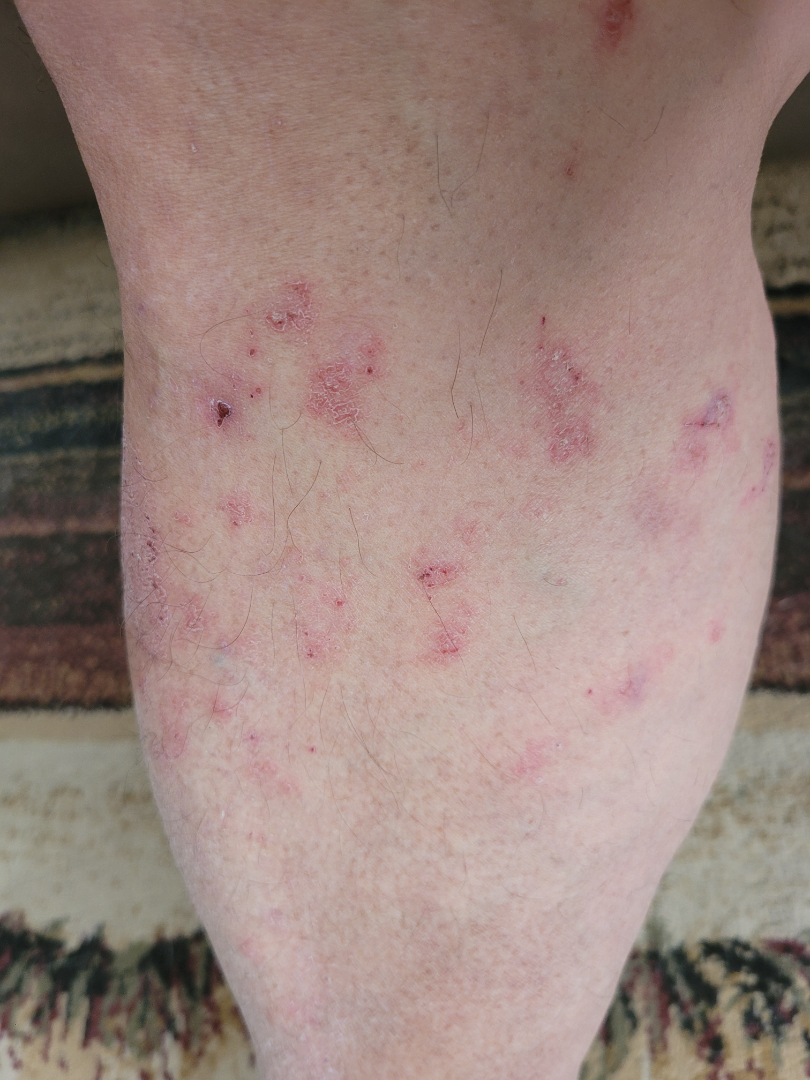• systemic symptoms: none reported
• contributor: male, age 60–69
• photo taken: at an angle
• described texture: raised or bumpy
• anatomic site: leg
• patient describes the issue as: a rash
• symptom duration: less than one week
• lesion symptoms: itching
• assessment: Eczema (0.67); Pityriasis lichenoides (0.33)